No constitutional symptoms were reported · the patient considered this a rash · the contributor is male · the photograph is a close-up of the affected area · the lesion involves the back of the torso · the patient indicates bothersome appearance — 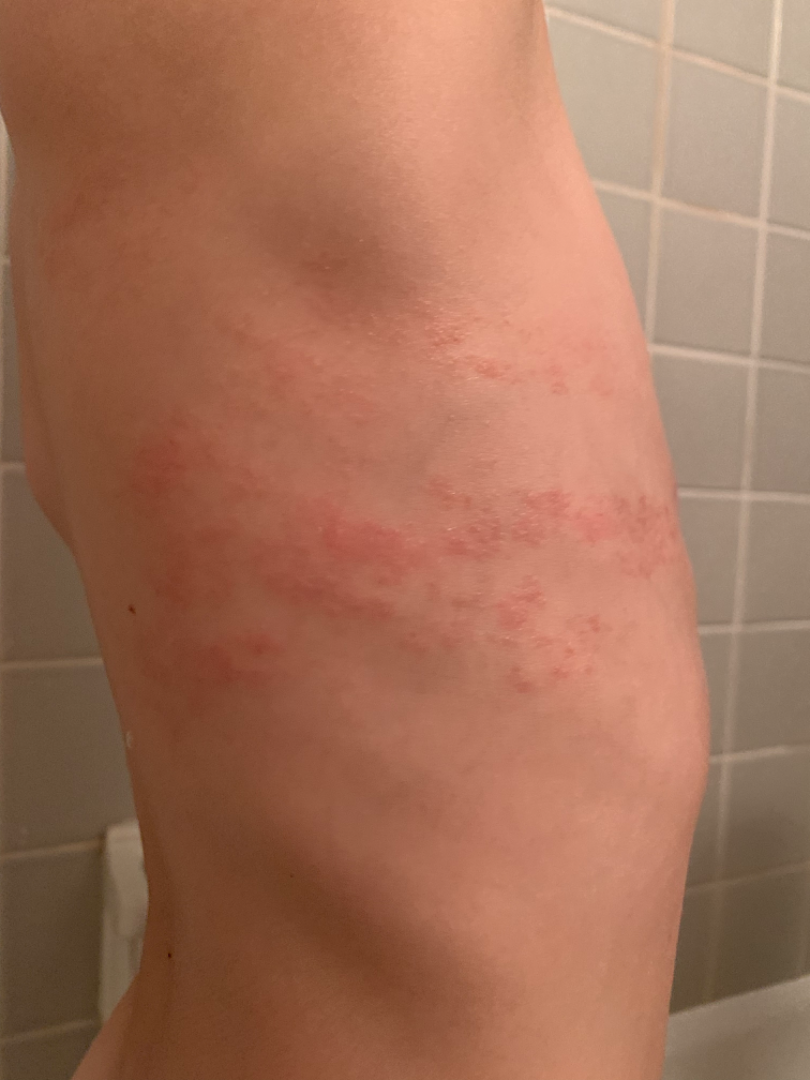| feature | finding |
|---|---|
| assessment | ungradable on photographic review |